The patient says their skin reddens with sun exposure. The patient describes having few moles overall. A male patient 72 years of age. Collected as part of a research study, without a referral diagnosis. The patient reports a personal history of cancer.
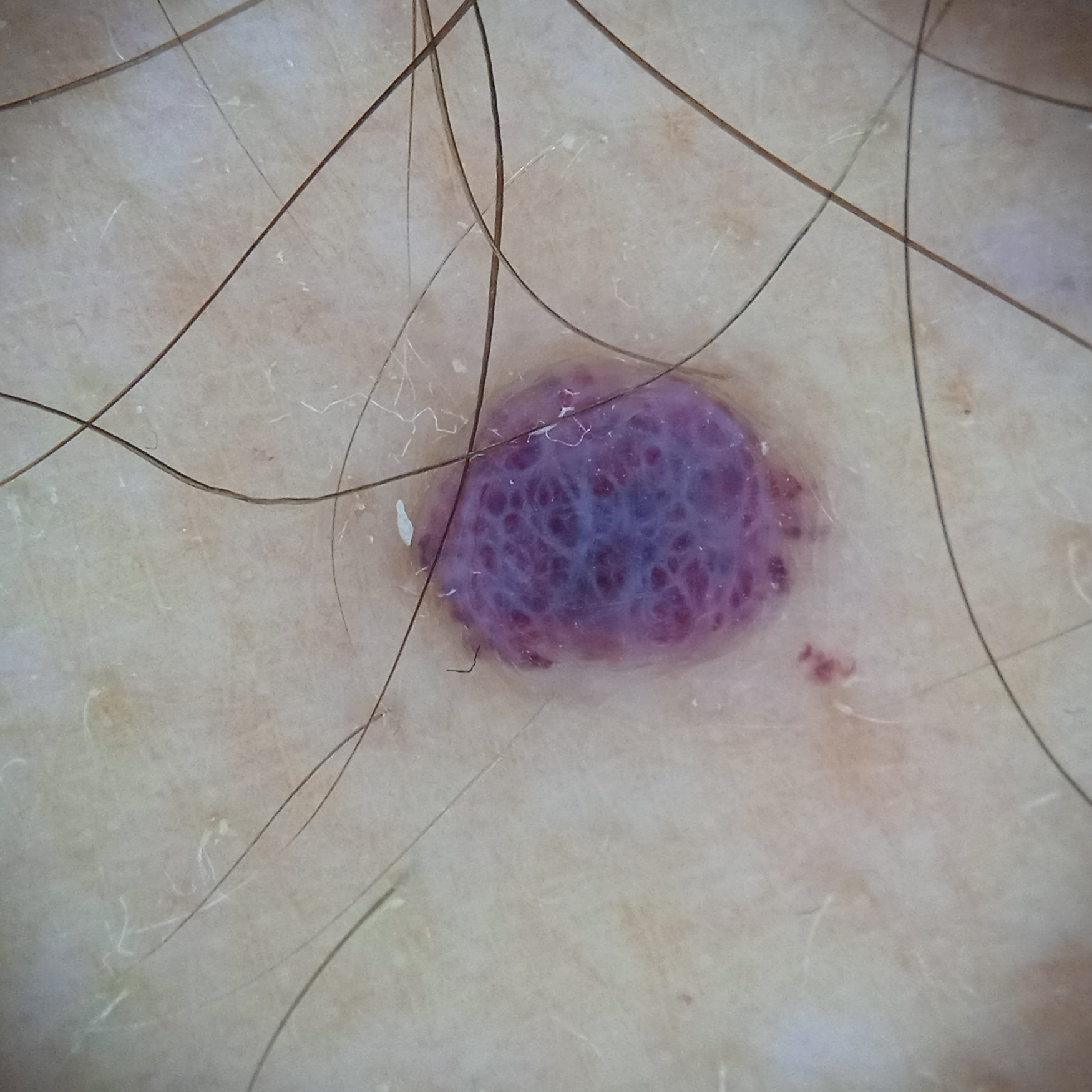anatomic site: the torso
lesion size: 4.7 mm
assessment: angioma (dermatologist consensus)